A clinical photo of a skin lesion taken with a smartphone.
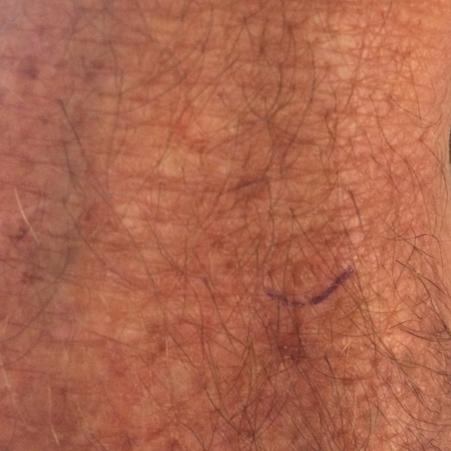Located on a forearm.
The patient describes that the lesion itches.
The clinical impression was an actinic keratosis.